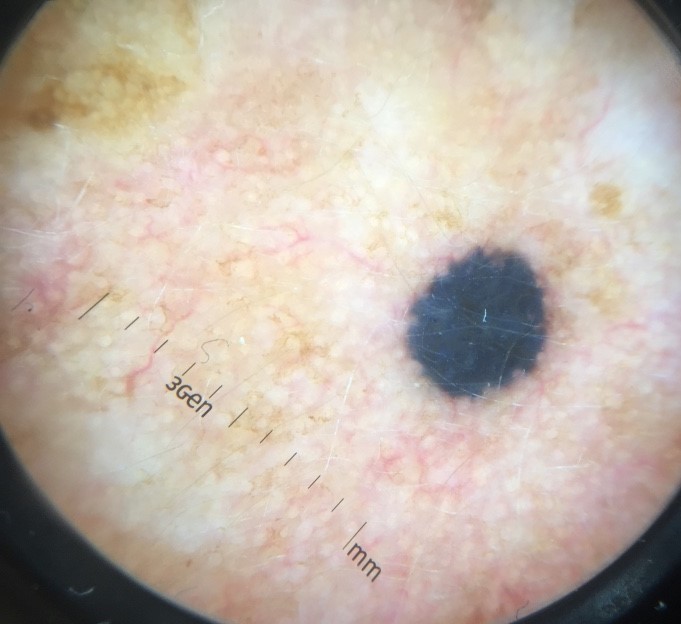<lesion>
<lesion_type>
<main_class>banal</main_class>
<pattern>dermal</pattern>
</lesion_type>
<diagnosis>
<name>blue nevus</name>
<code>bdb</code>
<malignancy>benign</malignancy>
<super_class>melanocytic</super_class>
<confirmation>expert consensus</confirmation>
</diagnosis>
</lesion>